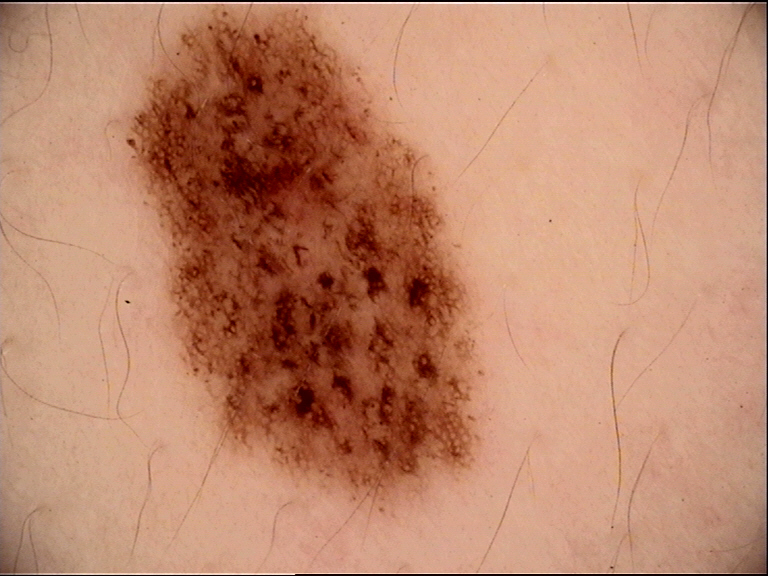Q: What is the diagnosis?
A: dysplastic junctional nevus (expert consensus)